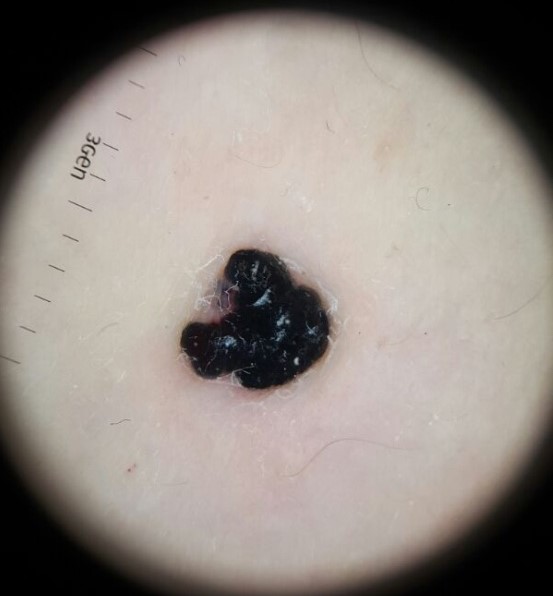modality — dermoscopy
classification — vascular
diagnostic label — angiokeratoma (expert consensus)